A dermoscopic close-up of a skin lesion: 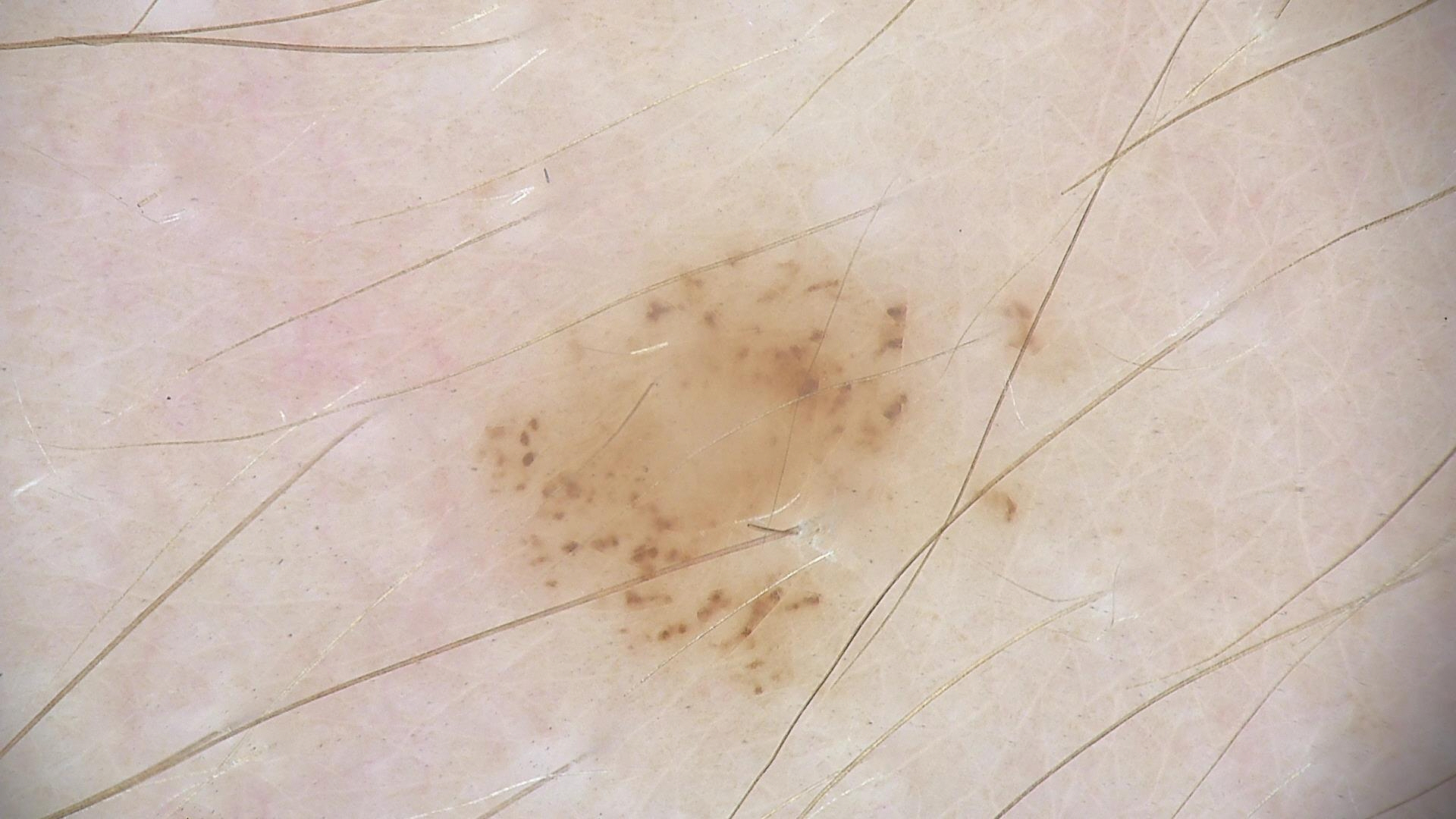| feature | finding |
|---|---|
| label | dysplastic junctional nevus (expert consensus) |